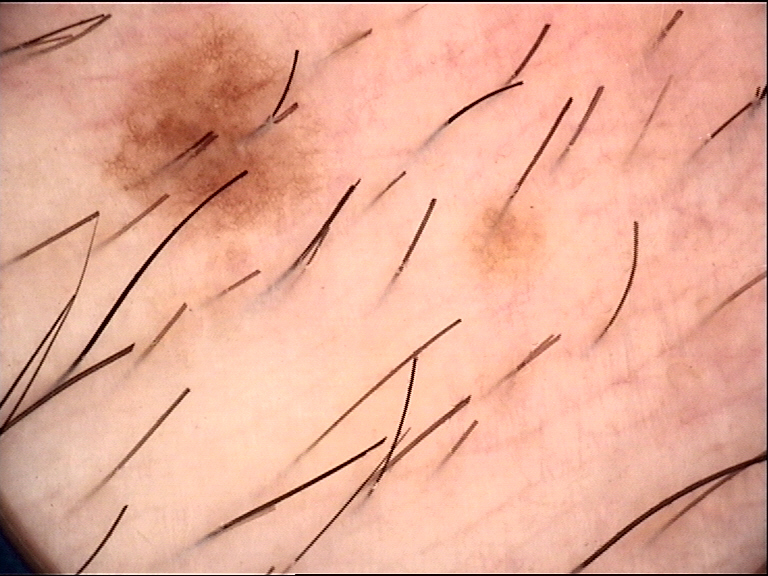{
  "image": "dermoscopy",
  "diagnosis": {
    "name": "dysplastic junctional nevus",
    "code": "jd",
    "malignancy": "benign",
    "super_class": "melanocytic",
    "confirmation": "expert consensus"
  }
}